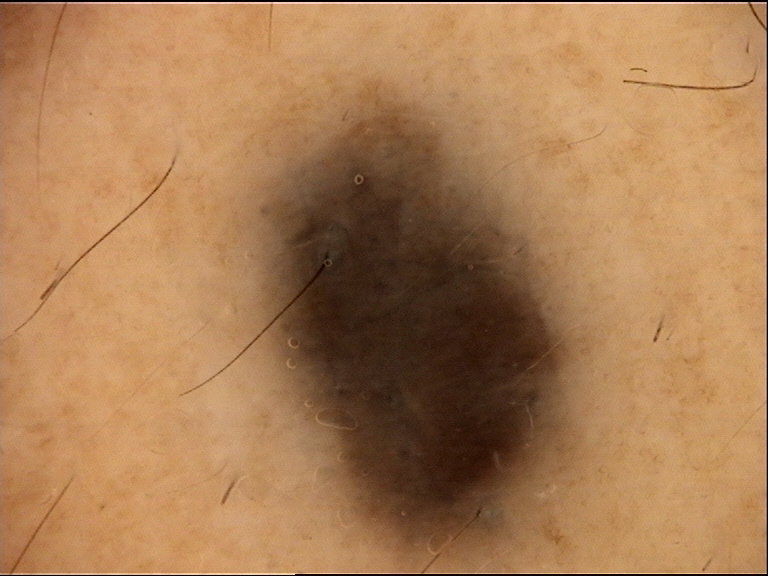A dermoscopic photograph of a skin lesion. Consistent with a dermal lesion — a blue nevus.